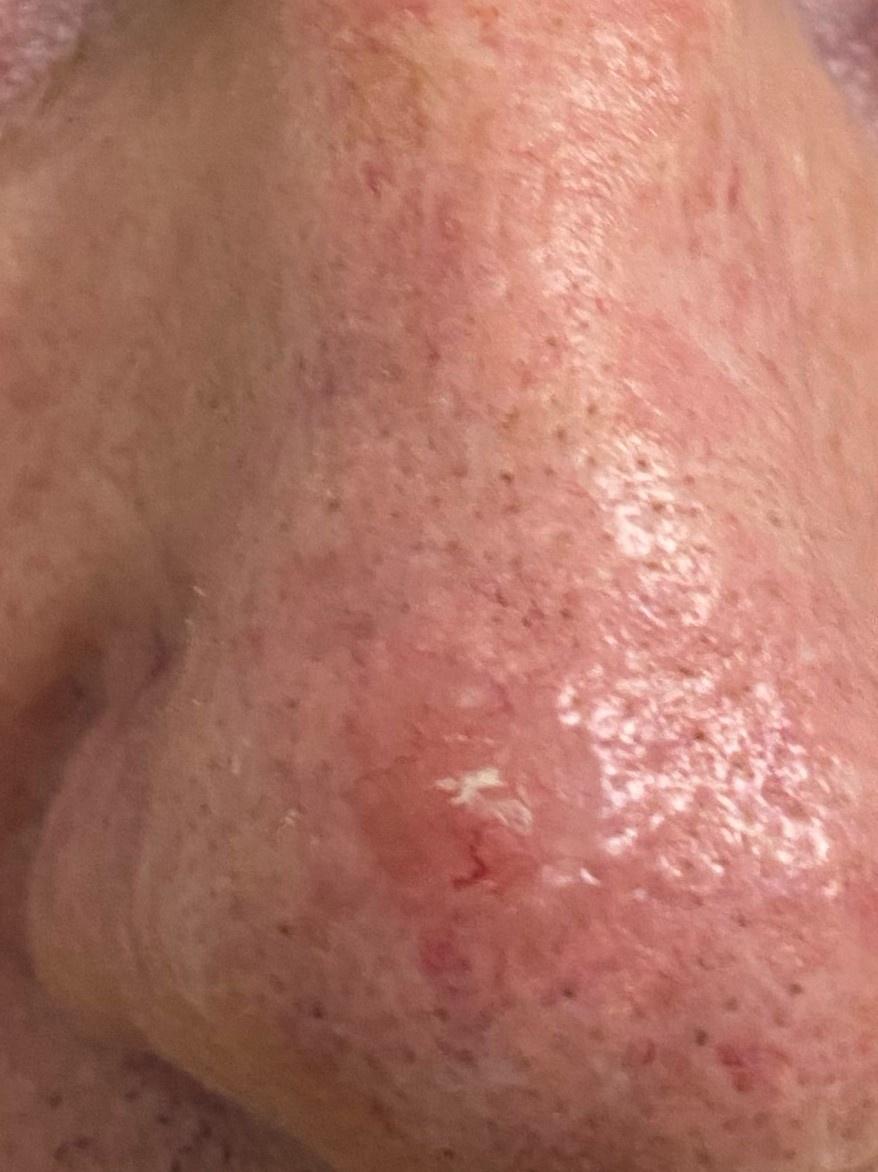Findings:
- diagnostic label · Basal cell carcinoma (biopsy-proven)